A dermoscopic image of a skin lesion.
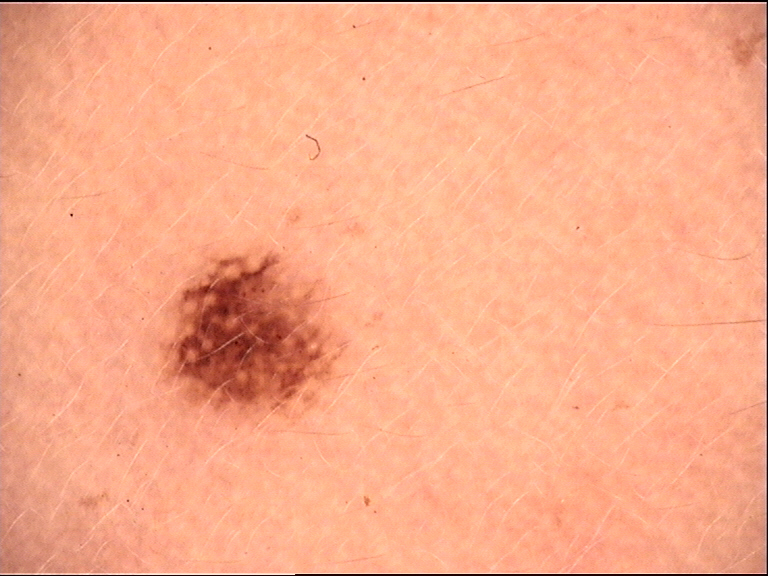diagnosis:
  name: Miescher nevus
  code: mcb
  malignancy: benign
  super_class: melanocytic
  confirmation: expert consensus